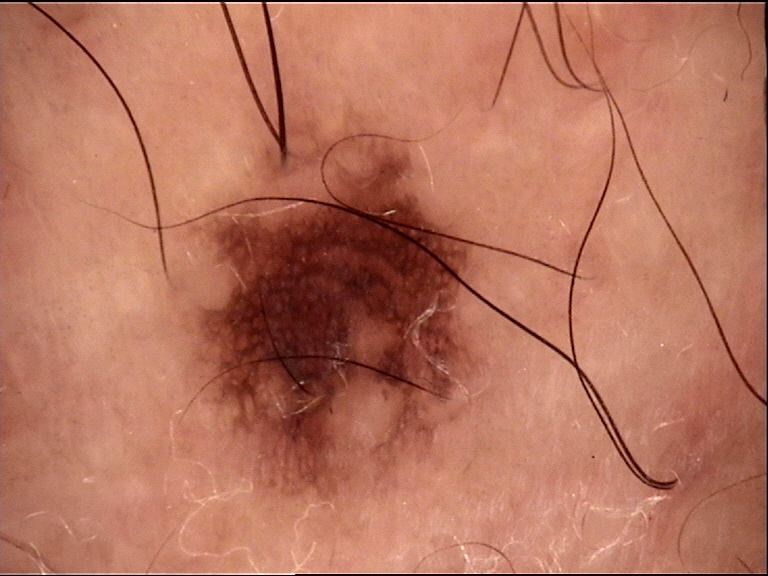imaging=dermoscopy | assessment=compound nevus (expert consensus).